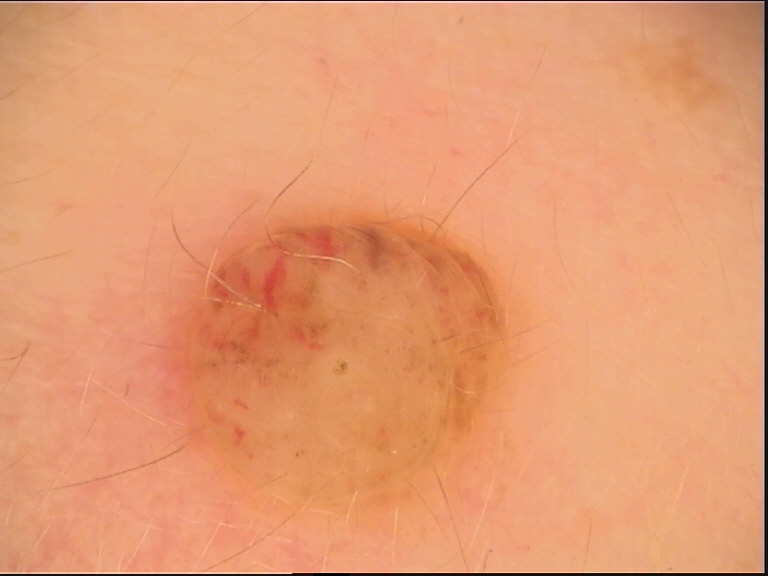{
  "diagnosis": {
    "name": "dermal nevus",
    "code": "db",
    "malignancy": "benign",
    "super_class": "melanocytic",
    "confirmation": "expert consensus"
  }
}